Per the chart, a previous melanoma. The patient was assessed as Fitzpatrick skin type II. Contact-polarized dermoscopy of a skin lesion. A female patient about 75 years old.
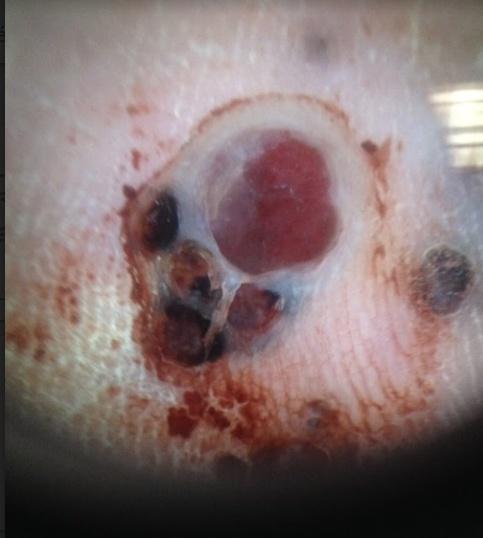Summary: Located on a lower extremity. Diagnosis: Histopathologically confirmed as a melanoma.